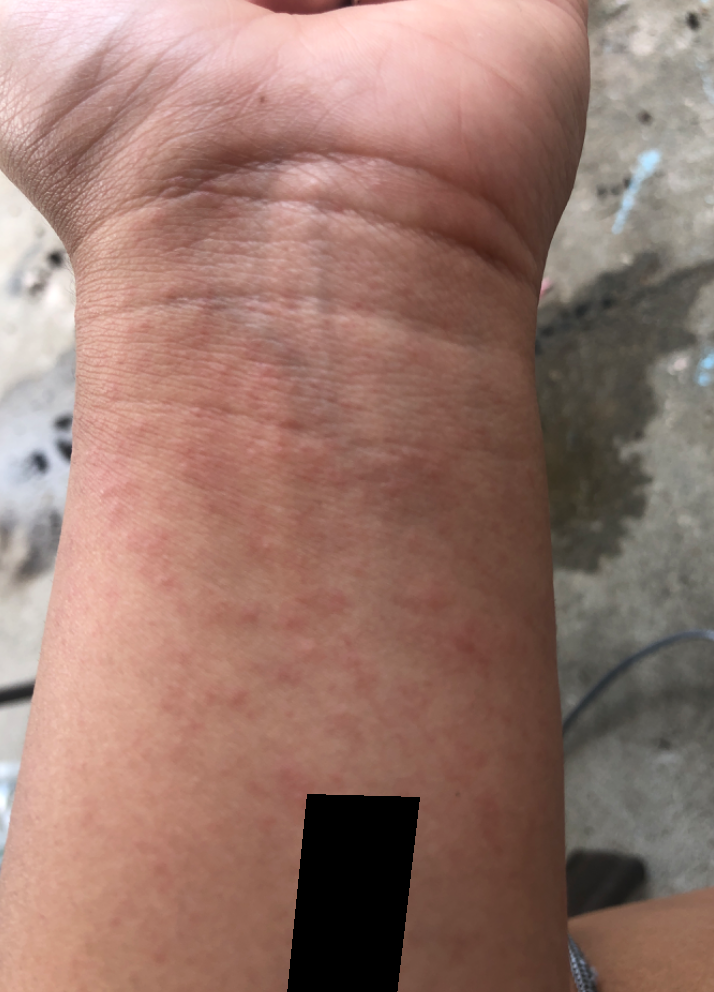The patient indicates itching and bothersome appearance. The patient indicates the lesion is raised or bumpy. The condition has been present for less than one week. The arm is involved. The contributor is 18–29, female. The photograph is a close-up of the affected area. On independent review by the dermatologists, the differential includes Acute dermatitis, NOS and Eczema, with no clear leading consideration; less probable is Drug Rash; less likely is Viral Exanthem; a remote consideration is Allergic Contact Dermatitis.